A dermoscopy image of a single skin lesion: 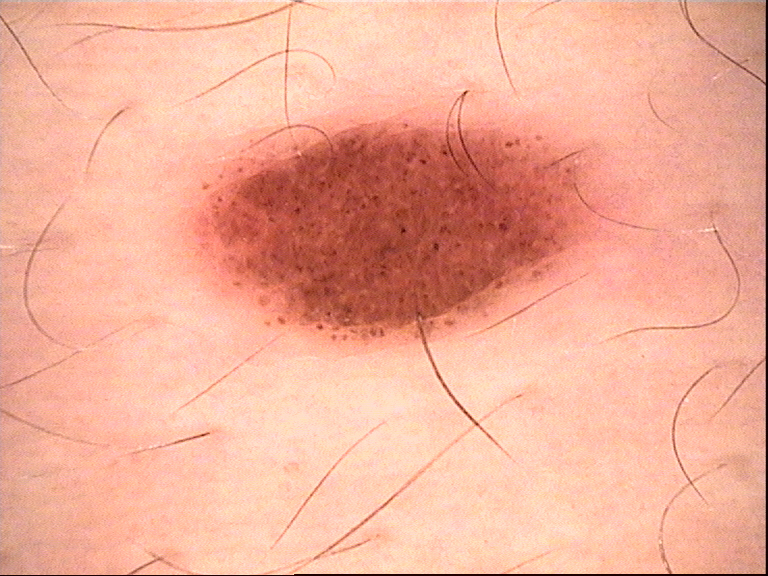The morphology is that of a banal lesion. Classified as a compound nevus.